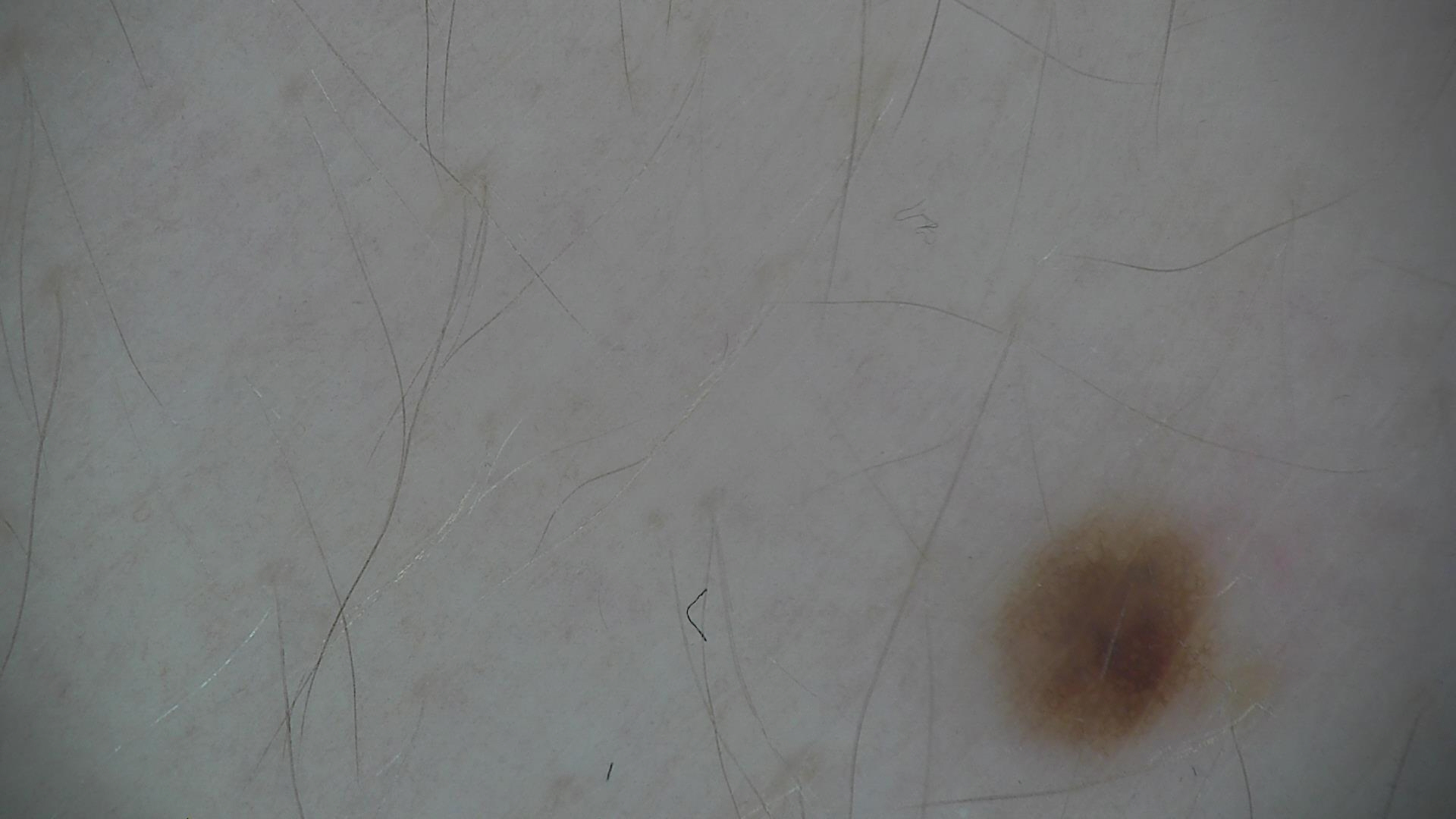A dermoscopic close-up of a skin lesion. Labeled as a dysplastic junctional nevus.